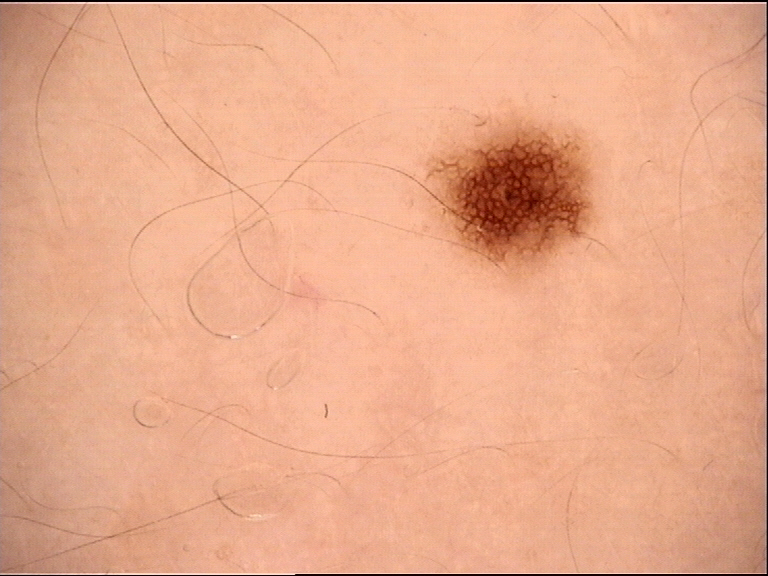Consistent with a junctional nevus.